A dermatoscopic image of a skin lesion.
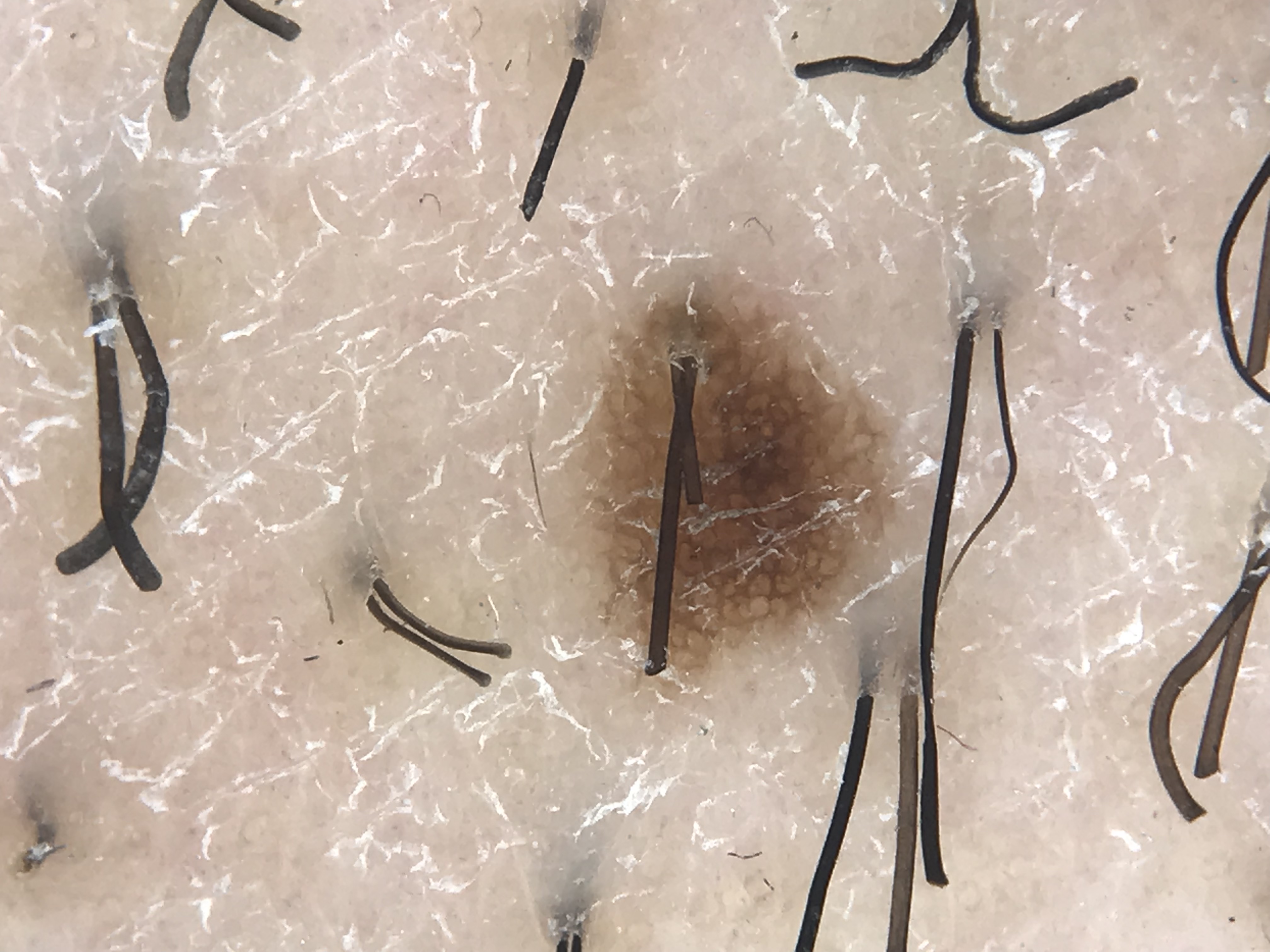Q: What is the diagnosis?
A: dysplastic junctional nevus (expert consensus)